A dermoscopic image of a skin lesion.
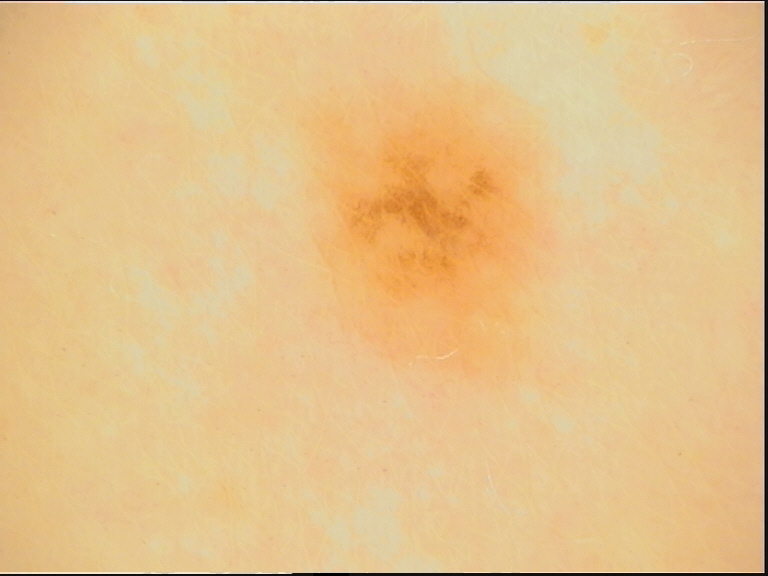Impression:
The diagnosis was a dysplastic junctional nevus.